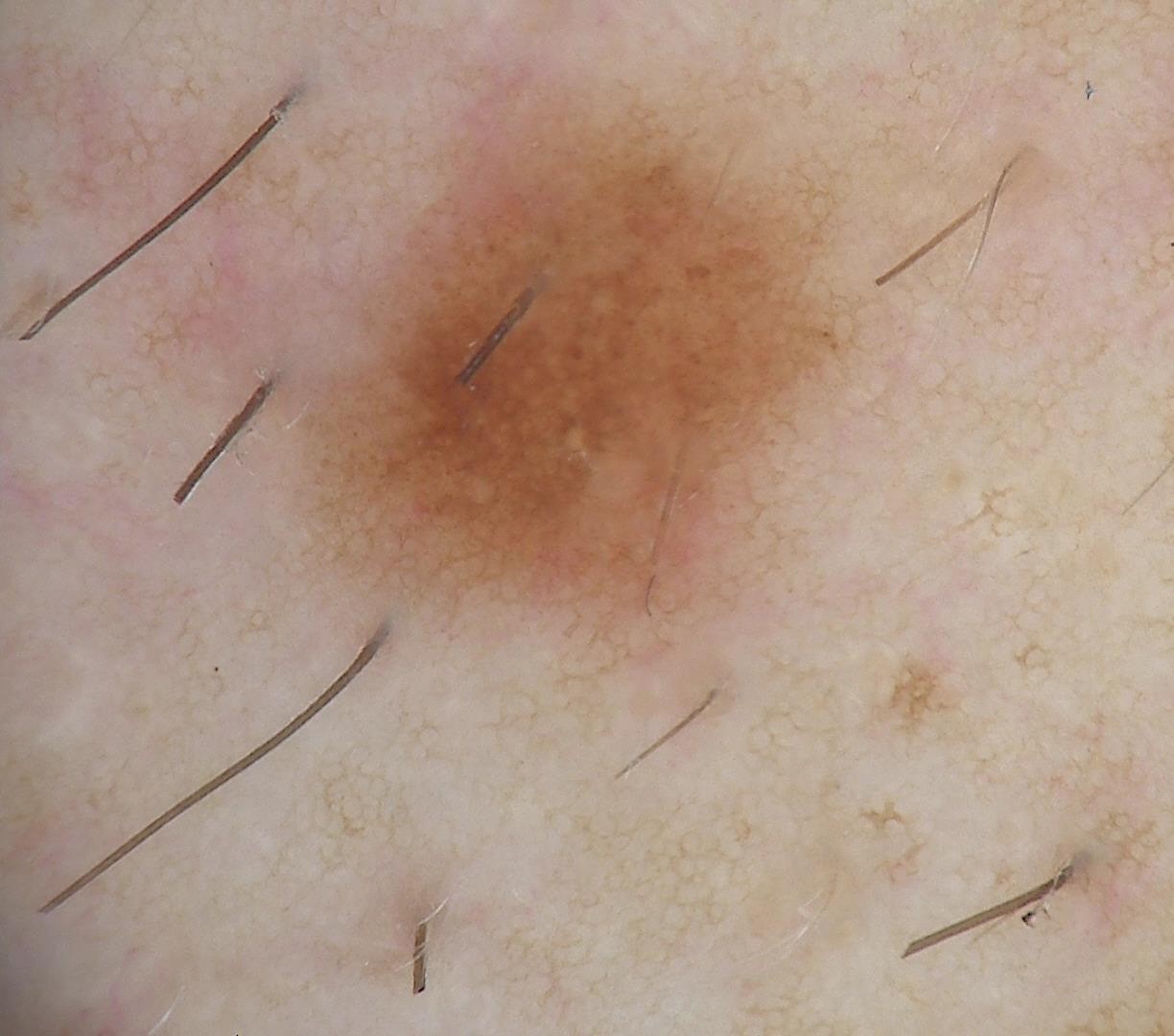diagnostic label — dysplastic junctional nevus (expert consensus).